A dermatoscopic image of a skin lesion. The patient is a female about 70 years old.
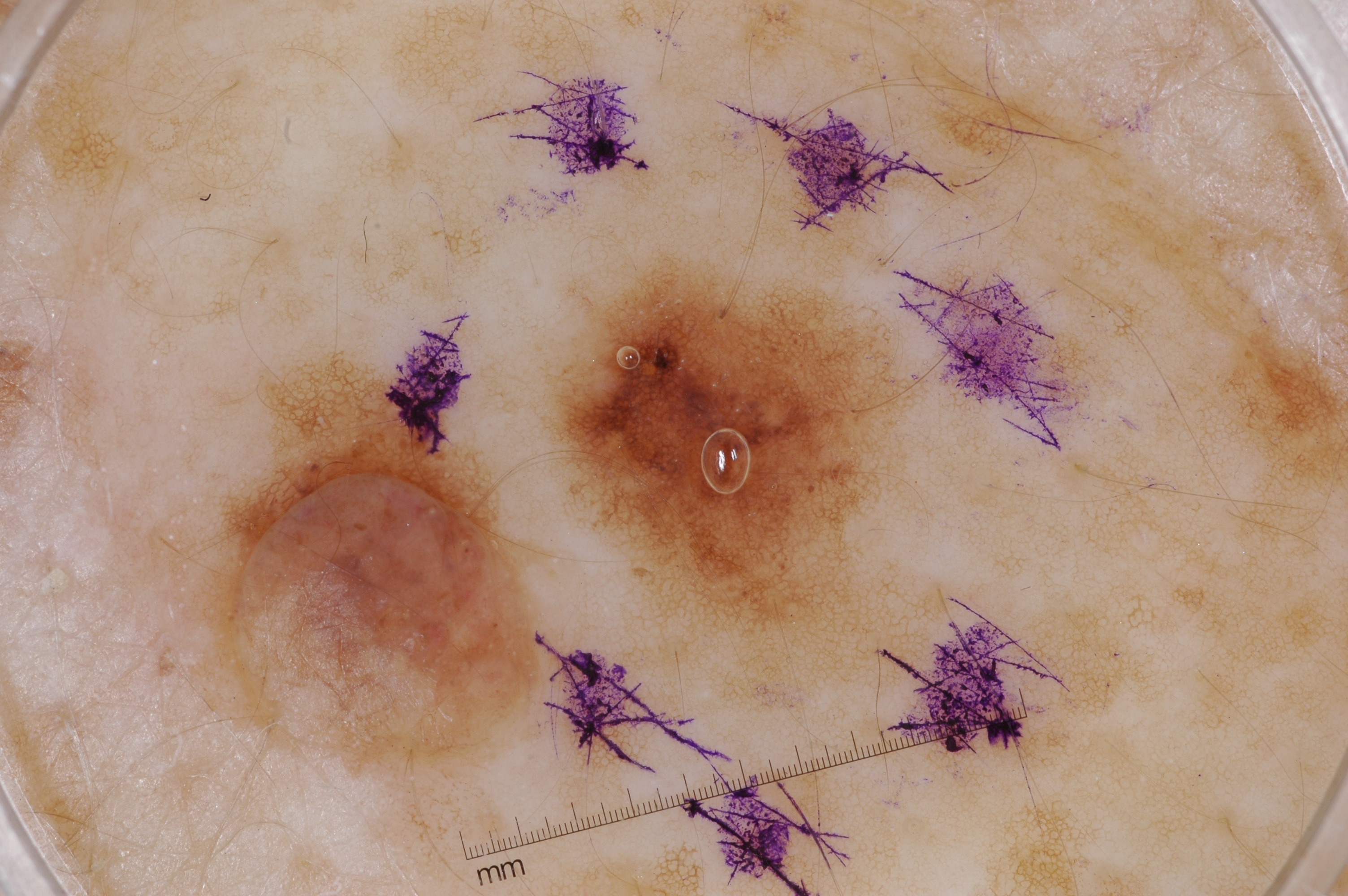Dermoscopy demonstrates milia-like cysts and pigment network; no streaks or negative network. A moderately sized lesion. In (x1, y1, x2, y2) order, the lesion is located at [502, 235, 986, 727]. Diagnosed as a melanocytic nevus, a benign skin lesion.